The patient described the issue as a rash; female patient, age 30–39; no relevant systemic symptoms; located on the arm; the patient indicates enlargement and itching; the photo was captured at an angle; the patient indicates the lesion is fluid-filled; the condition has been present for three to twelve months:
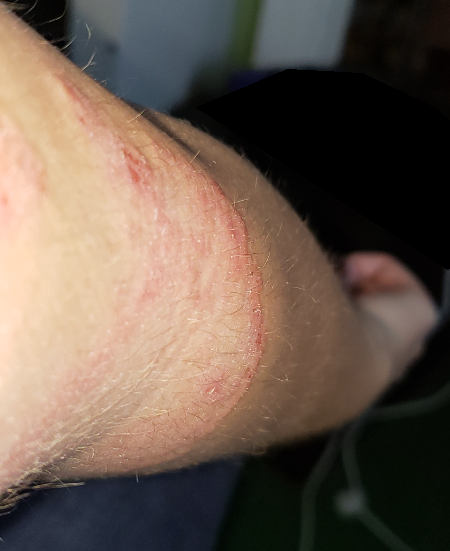Q: What is the differential diagnosis?
A: three dermatologists each reviewed the case: the primary impression is Tinea; a remote consideration is Annular erythema; less likely is Eczema; lower on the differential is Erythema annulare centrifugum; less probable is Erythema gyratum repens